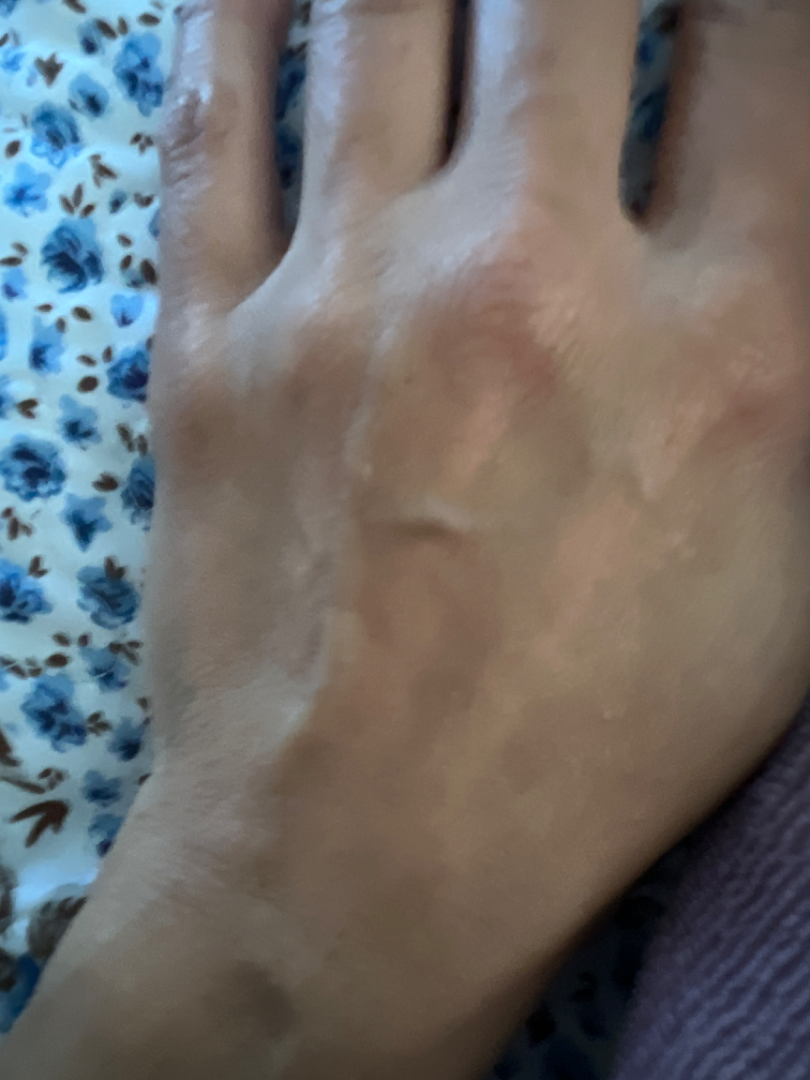The reviewing dermatologist was unable to assign a differential diagnosis from the image.